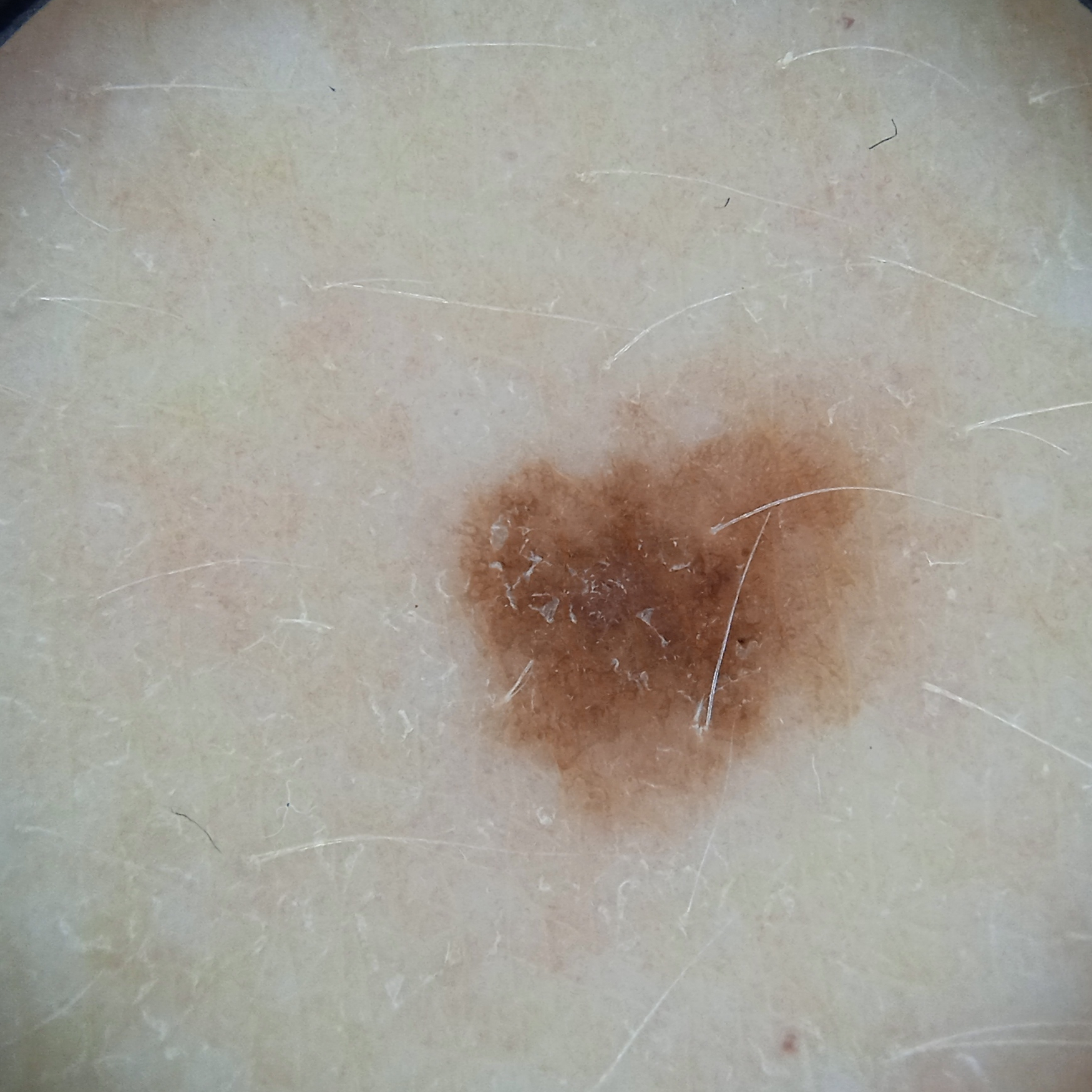Q: What is the referral context?
A: research study (no referral diagnosis)
Q: Tell me about the patient.
A: female, aged 50
Q: What is the patient's nevus burden?
A: a moderate number of melanocytic nevi
Q: Where is the lesion?
A: the torso
Q: Lesion size?
A: 5.4 mm
Q: What was the diagnosis?
A: melanocytic nevus (dermatologist consensus)